A skin lesion imaged with a dermatoscope; a female subject, aged 58 to 62.
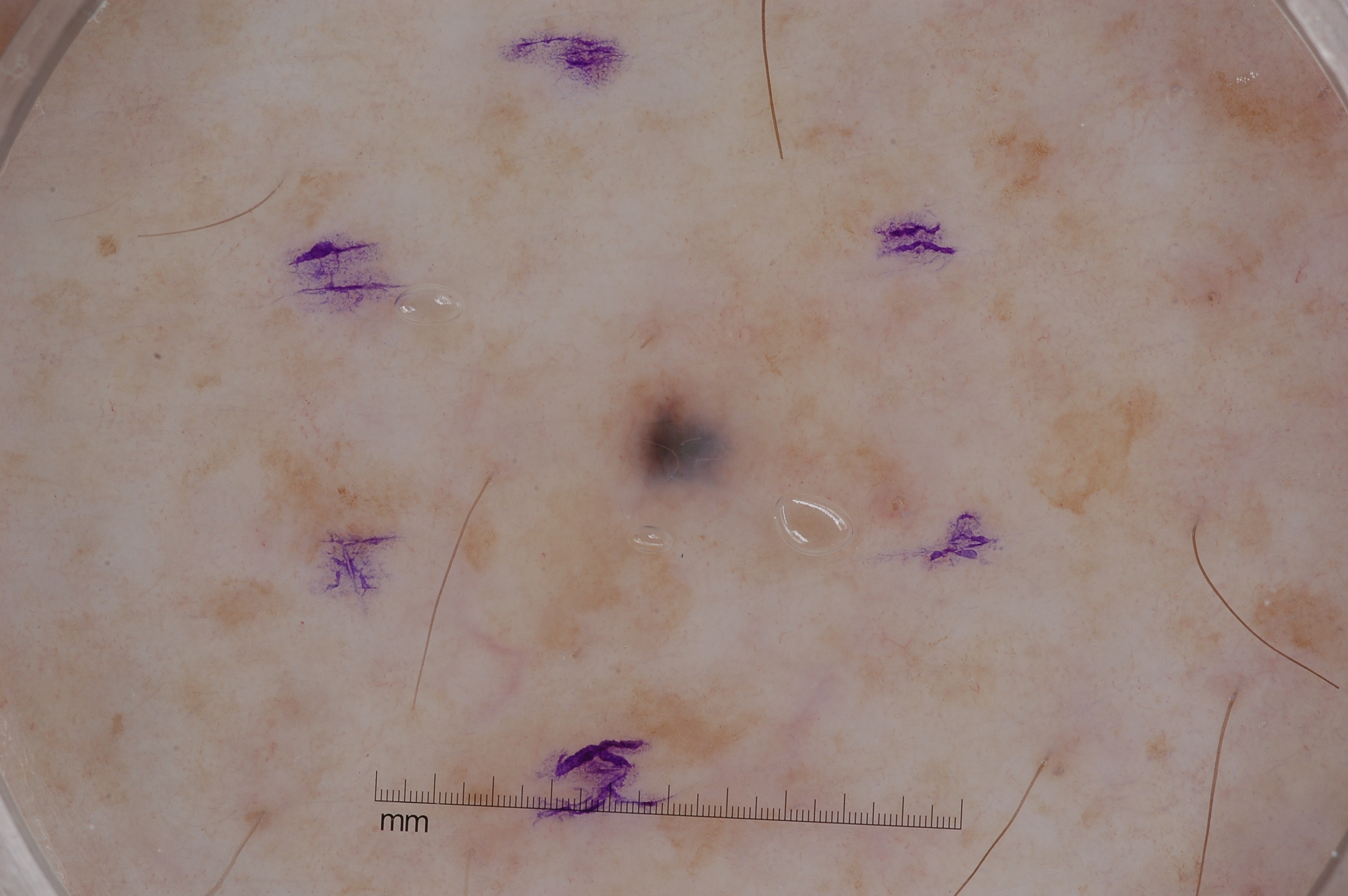Image and clinical context: The lesion is bounded by [601,364,716,469]. Dermoscopic examination shows no negative network, milia-like cysts, streaks, or pigment network. Assessment: Clinically diagnosed as a melanocytic nevus.